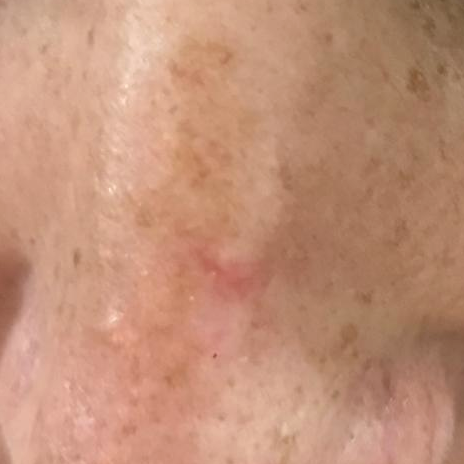Q: What is the imaging modality?
A: clinical photo
Q: Where on the body is the lesion?
A: the nose
Q: What is the diagnosis?
A: actinic keratosis (clinical consensus)